A dermoscopic photograph of a skin lesion: 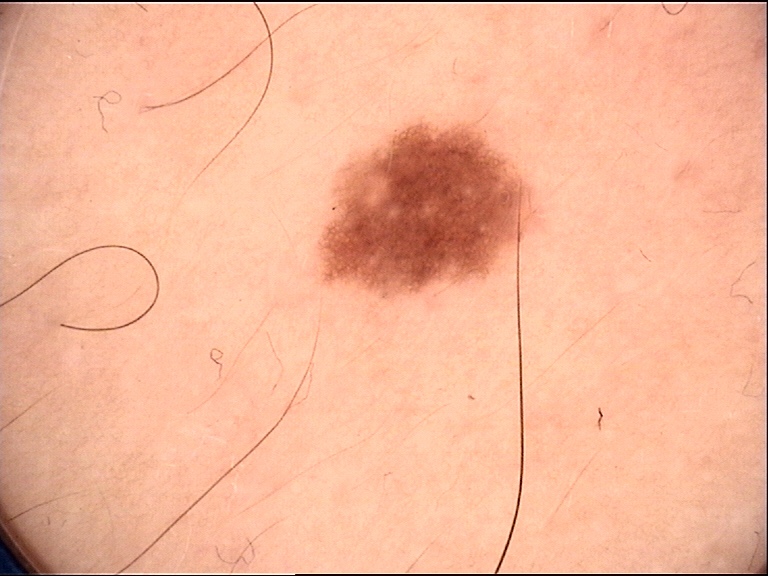| field | value |
|---|---|
| diagnosis | dysplastic junctional nevus (expert consensus) |